A skin lesion imaged with a dermatoscope: 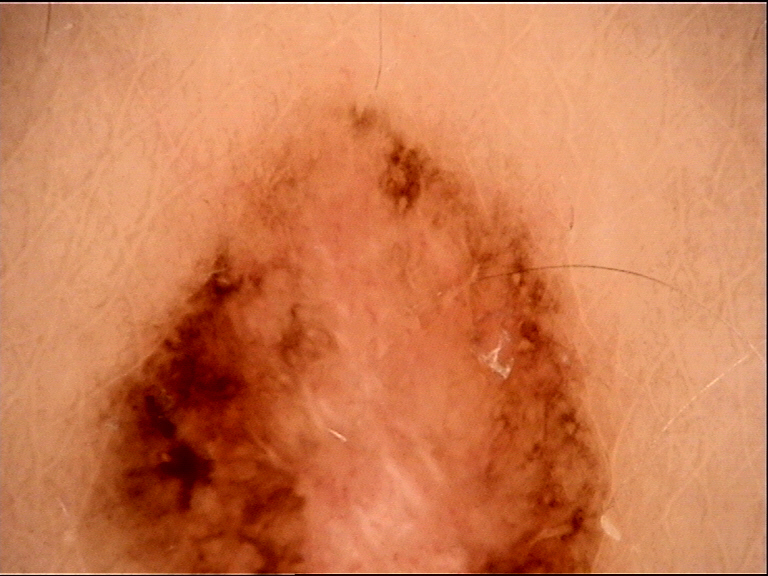Confirmed on histopathology as a melanoma.